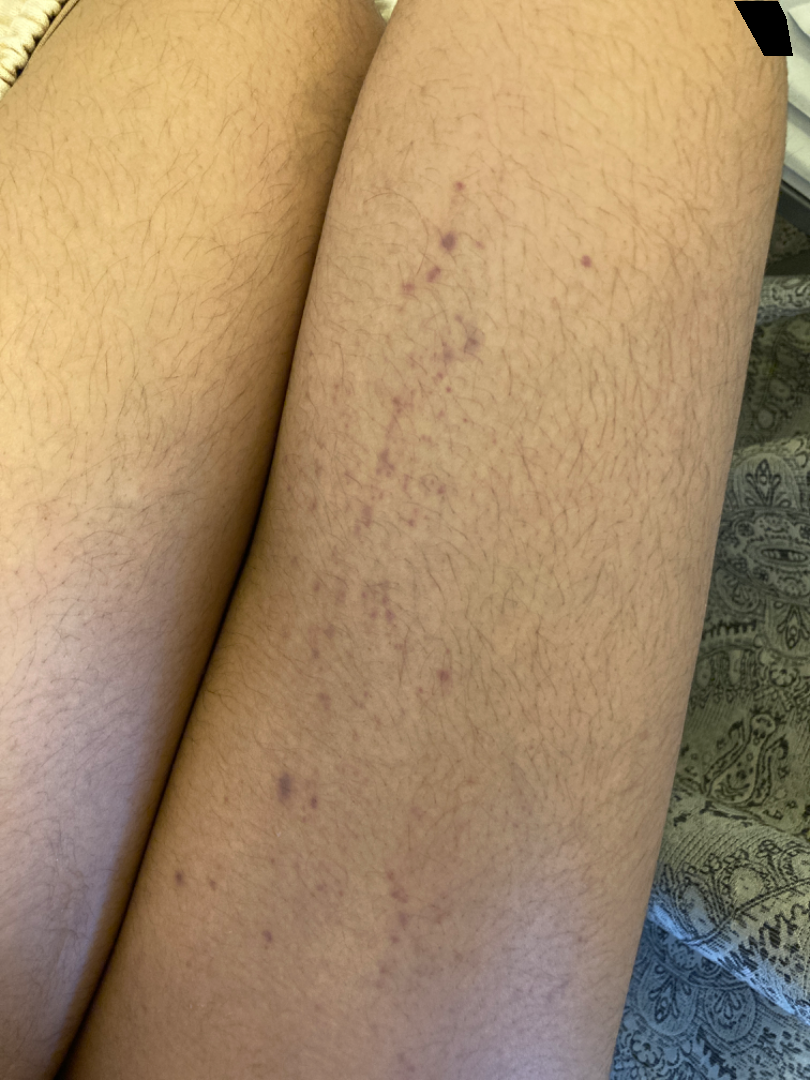differential = reviewed remotely by one dermatologist: Contact purpura, Lichen planus/lichenoid eruption and Pigmented purpuric eruption were considered with similar weight.